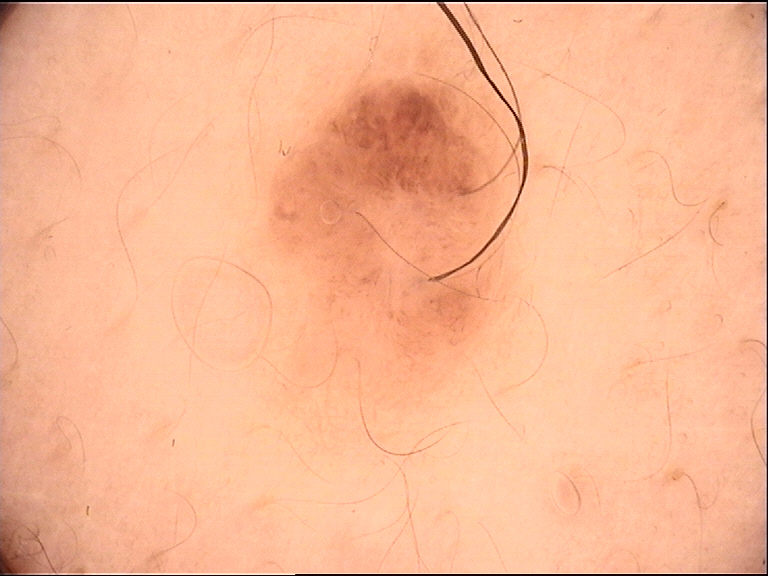classification: banal | diagnostic label: dermal nevus (expert consensus).